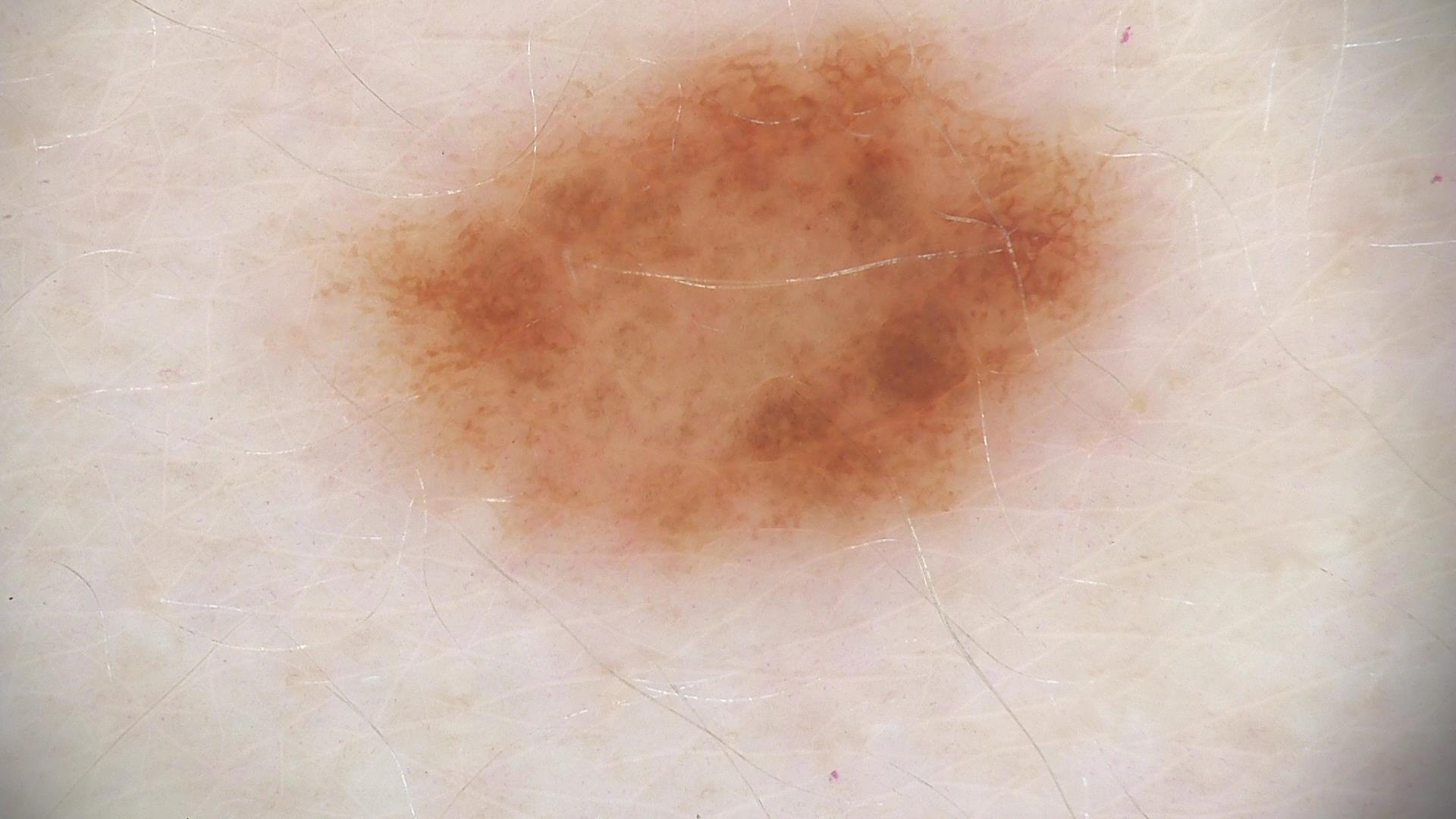Dermoscopy of a skin lesion. Consistent with a benign lesion — a dysplastic junctional nevus.